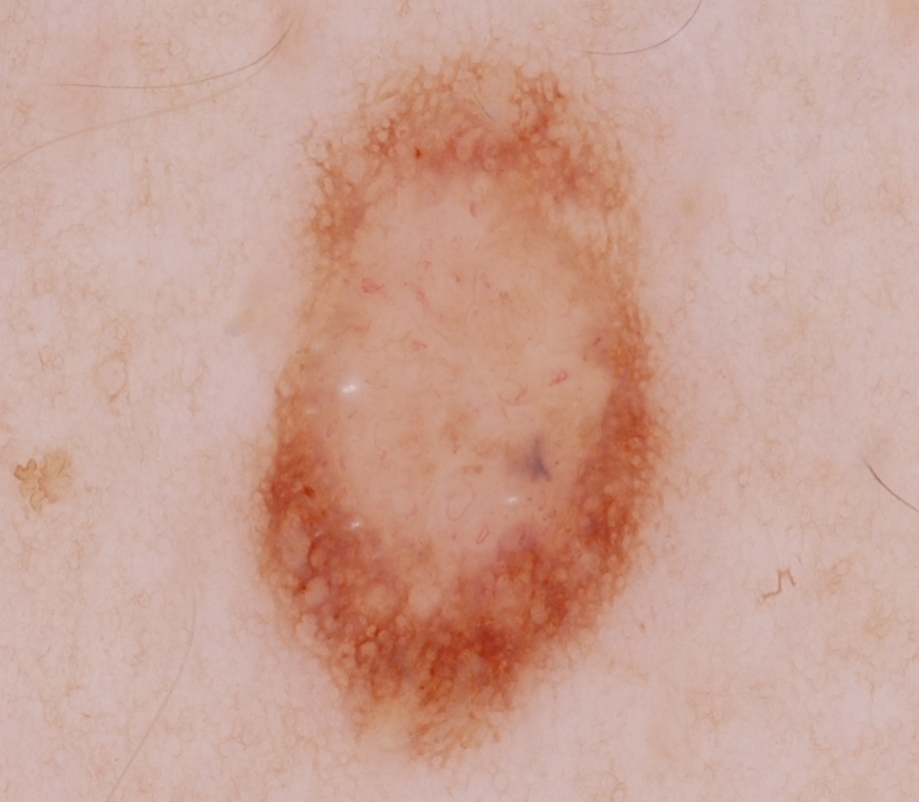Case summary: This is a dermoscopic photograph of a skin lesion. The lesion spans x1=246 y1=52 x2=682 y2=757. The lesion occupies roughly 30% of the field. Dermoscopically, the lesion shows milia-like cysts and pigment network. Impression: The clinical diagnosis was a melanocytic nevus, a benign lesion.